The subject is a female aged 30–39; the lesion involves the arm and front of the torso; an image taken at a distance.
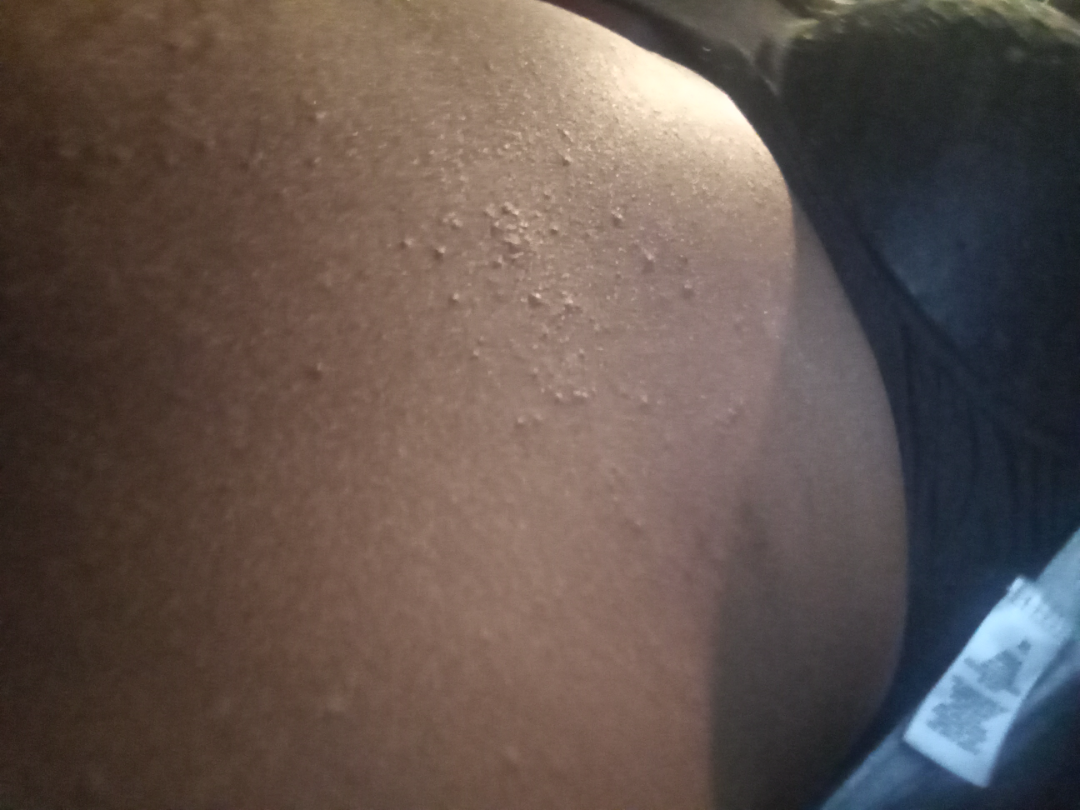The reviewer was unable to grade this case for skin condition. The patient notes the lesion is rough or flaky and raised or bumpy.